The photograph is a close-up of the affected area. The subject is 30–39, male. The affected area is the top or side of the foot: 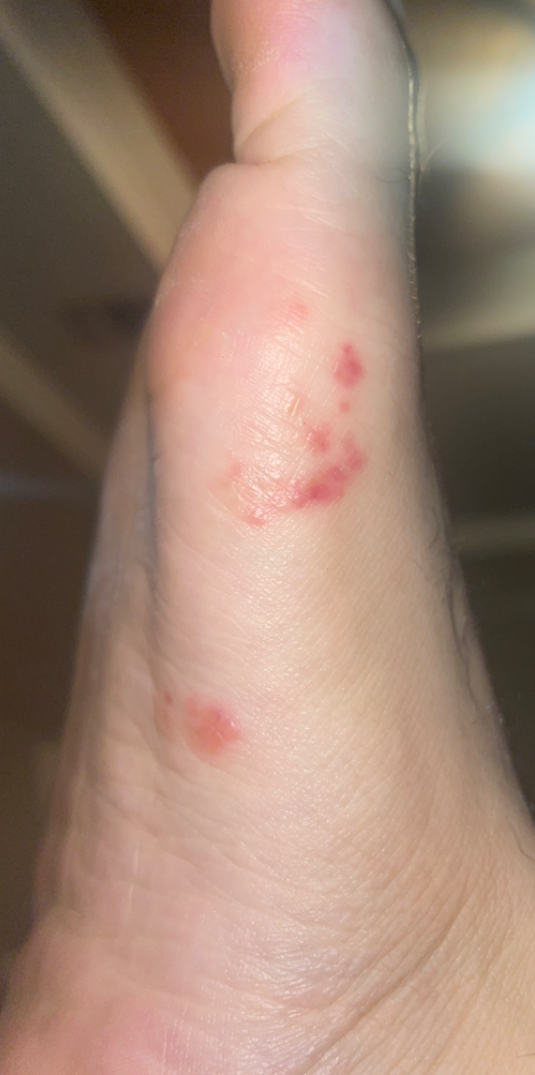{"differential": {"leading": ["Eczema"], "considered": ["Herpes Zoster", "Cutaneous larva migrans"]}}